A dermatoscopic image of a skin lesion: 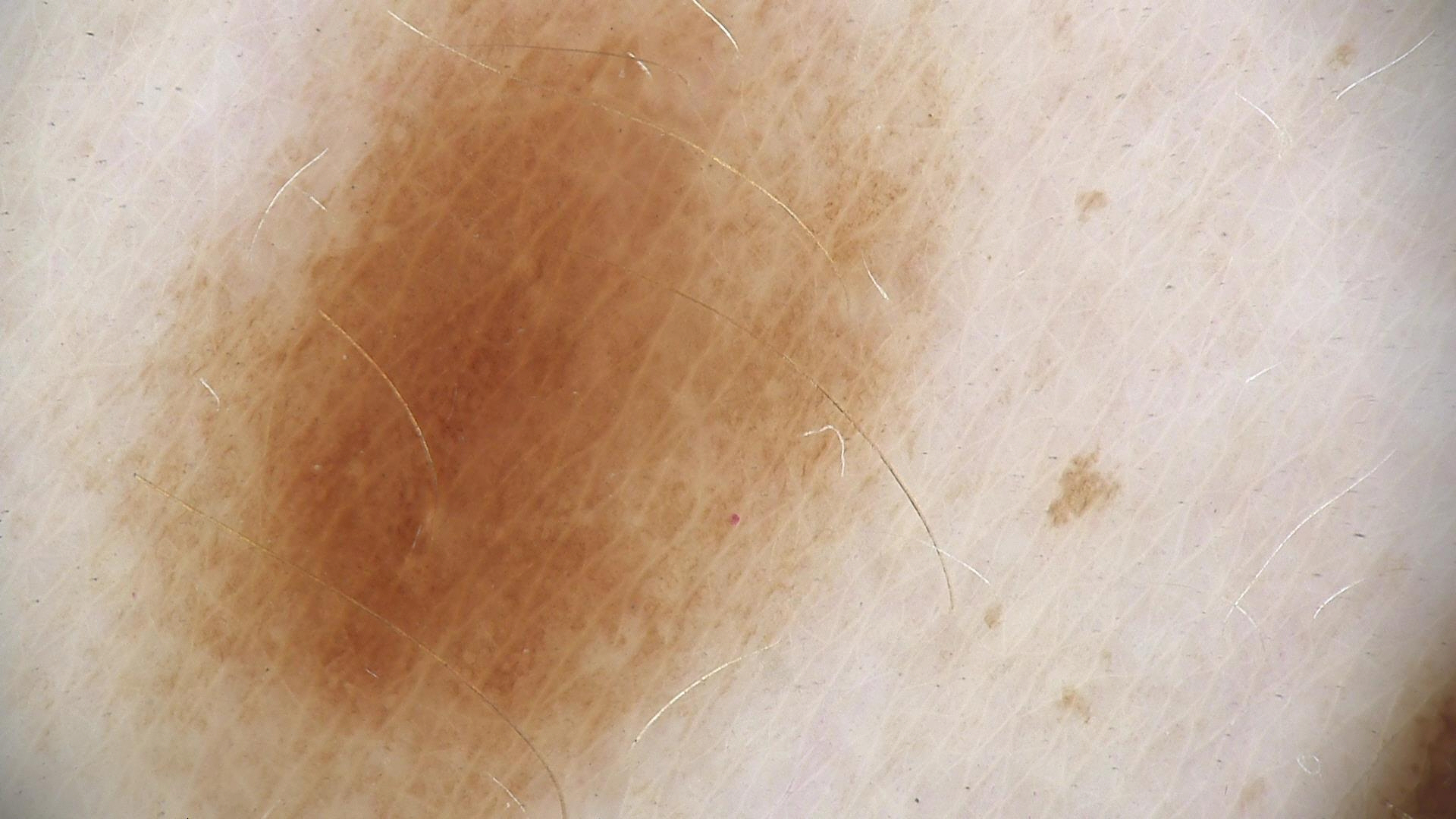| feature | finding |
|---|---|
| assessment | dysplastic junctional nevus (expert consensus) |